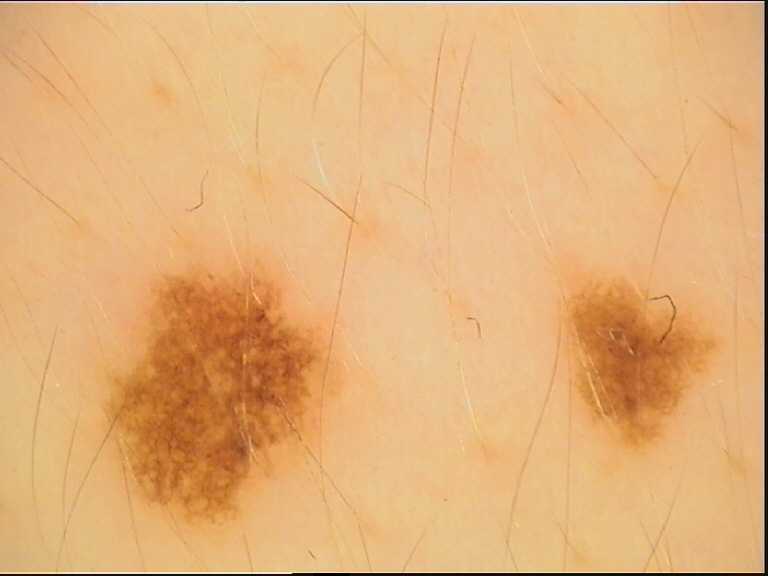Impression:
The diagnostic label was a dysplastic junctional nevus.